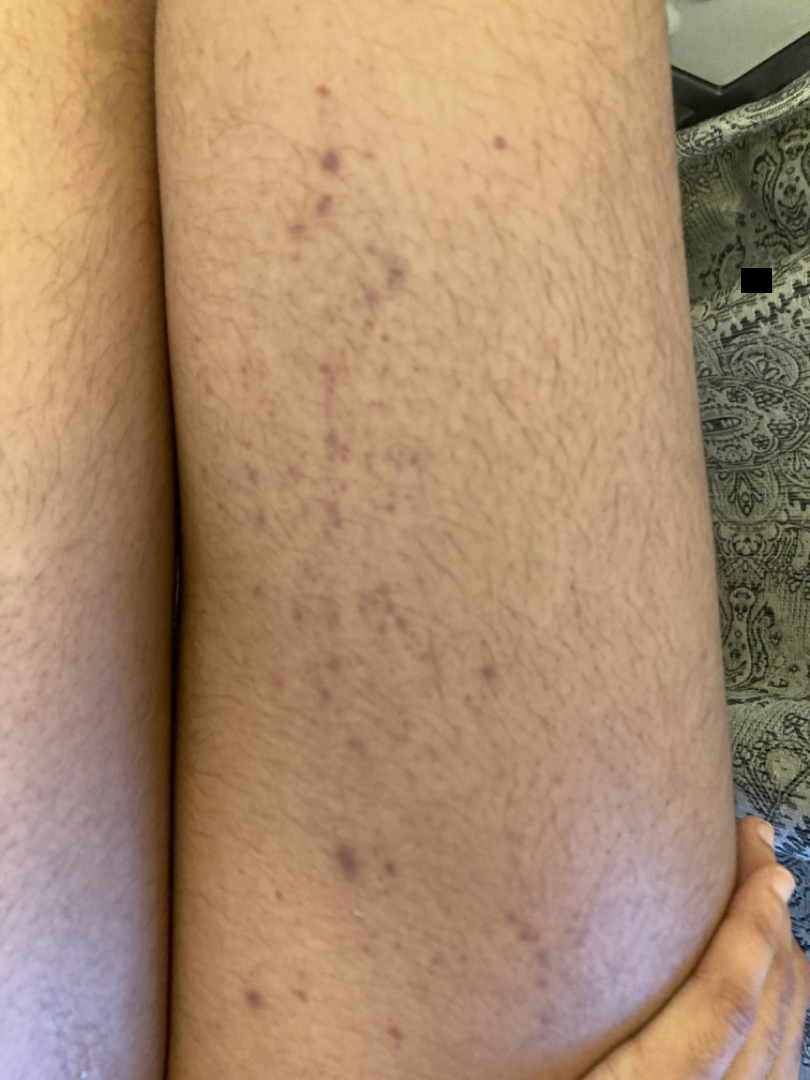site: leg | patient-reported symptoms: darkening, enlargement and itching | shot type: close-up | patient describes the issue as: a rash | surface texture: flat | clinical impression: the differential, in no particular order, includes Contact purpura, Lichen planus/lichenoid eruption and Pigmented purpuric eruption.